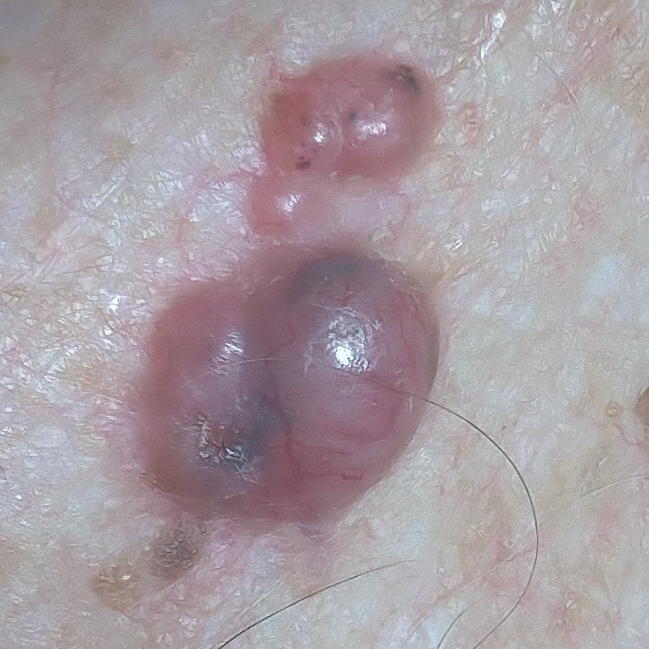image = clinical photo; subject = male, in their late 70s; location = the chest; reported symptoms = elevation, growth, itching / no change in appearance, no bleeding; diagnostic label = basal cell carcinoma (biopsy-proven).